The patient was assessed as Fitzpatrick phototype II; by history, alcohol use, pesticide exposure, and no prior skin cancer (patient or family); a clinical photograph of a skin lesion; a male patient in their early 30s: 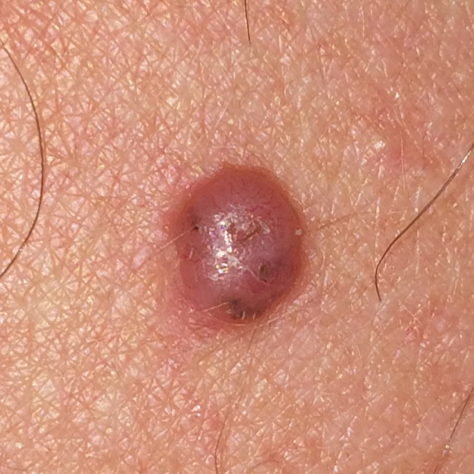The lesion involves the back.
The lesion measures 6 × 4 mm.
The patient reports that the lesion hurts, is elevated, has grown, and itches.
Histopathology confirmed a malignancy — a basal cell carcinoma.